A close-up photograph; the lesion involves the leg; the patient is a female aged 40–49: 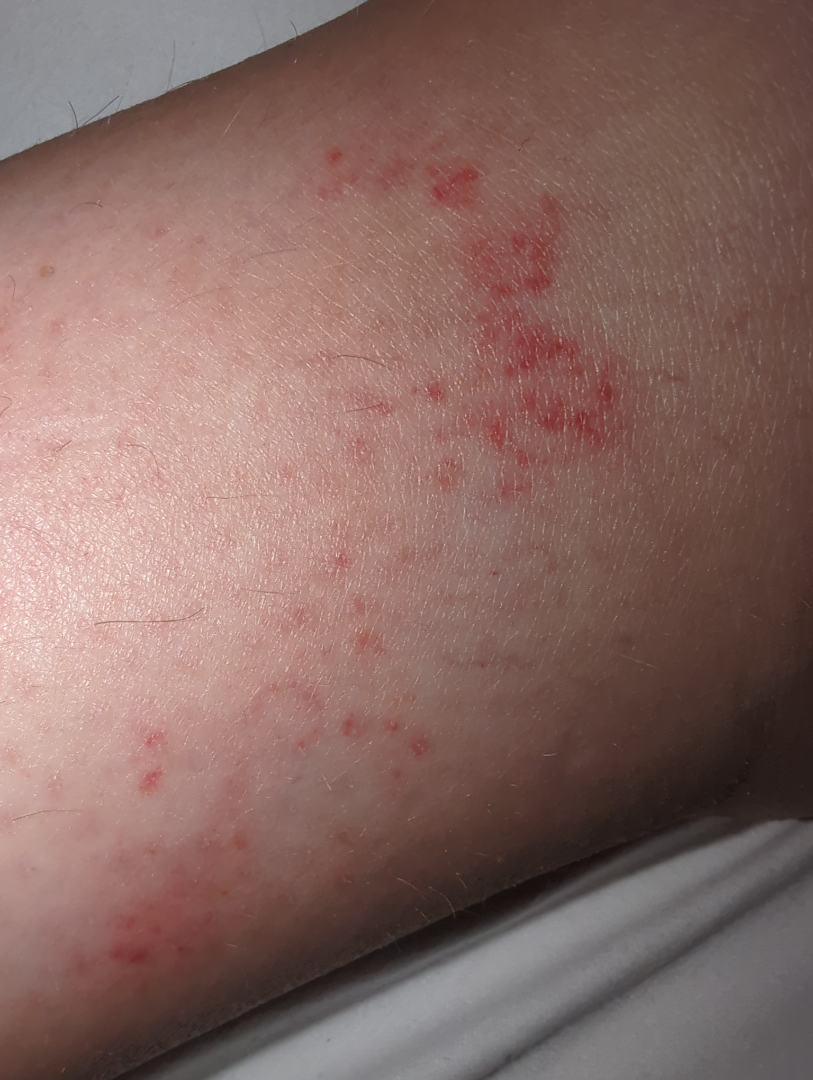  differential:
    tied_lead:
      - Eczema
      - Irritant Contact Dermatitis